The contributor is a female aged 40–49; located on the leg; reported duration is about one day; this is a close-up image; Fitzpatrick III; no associated lesion symptoms were reported; the lesion is described as flat: 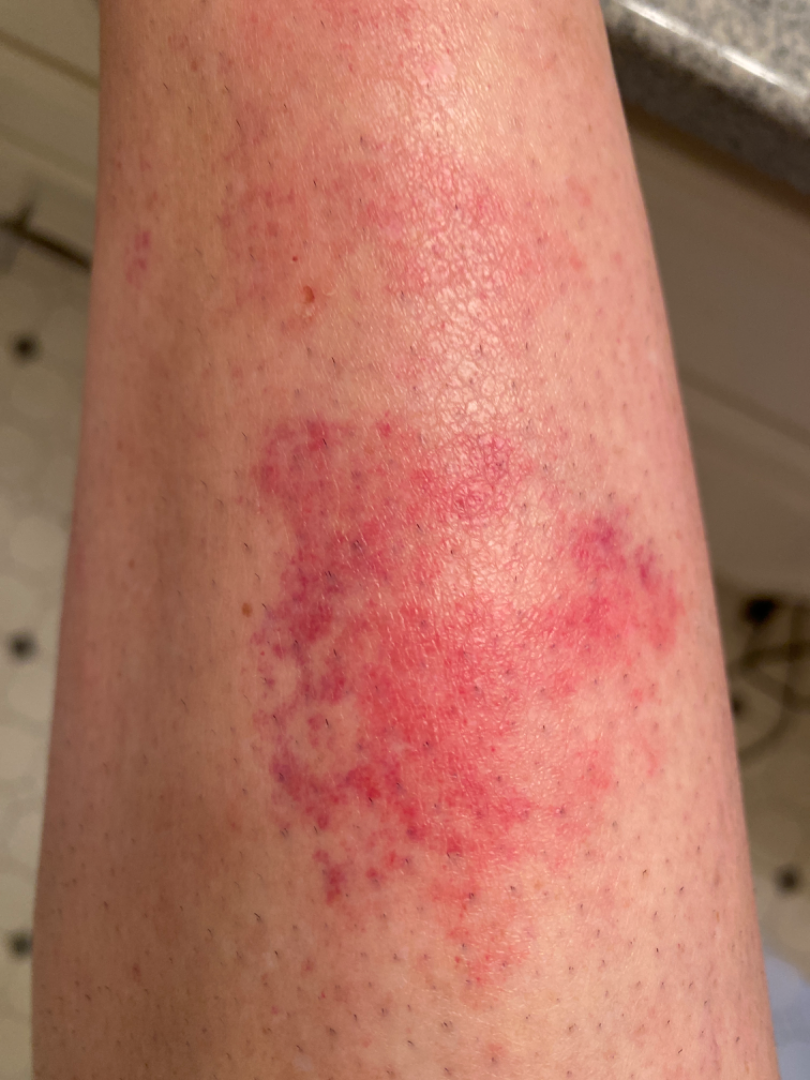clinical impression = single-reviewer assessment: most consistent with Acute dermatitis, NOS